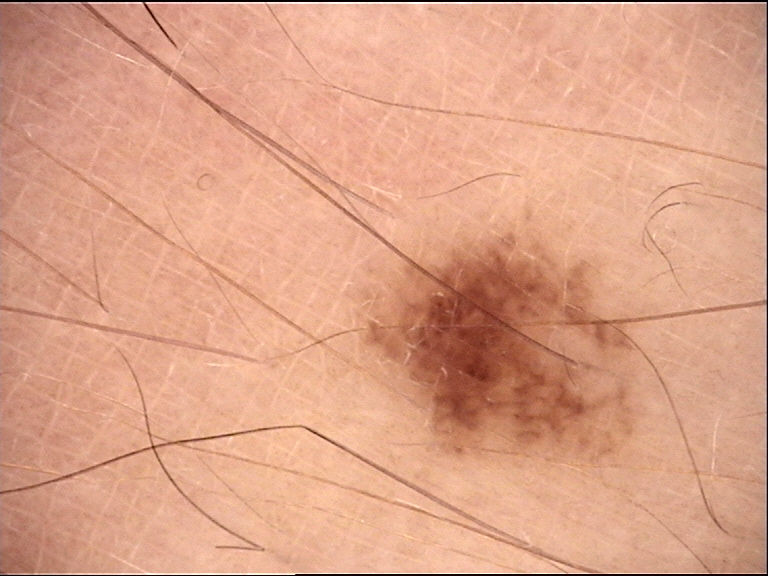image: dermoscopy | diagnosis: junctional nevus (expert consensus).